A dermatoscopic image of a skin lesion.
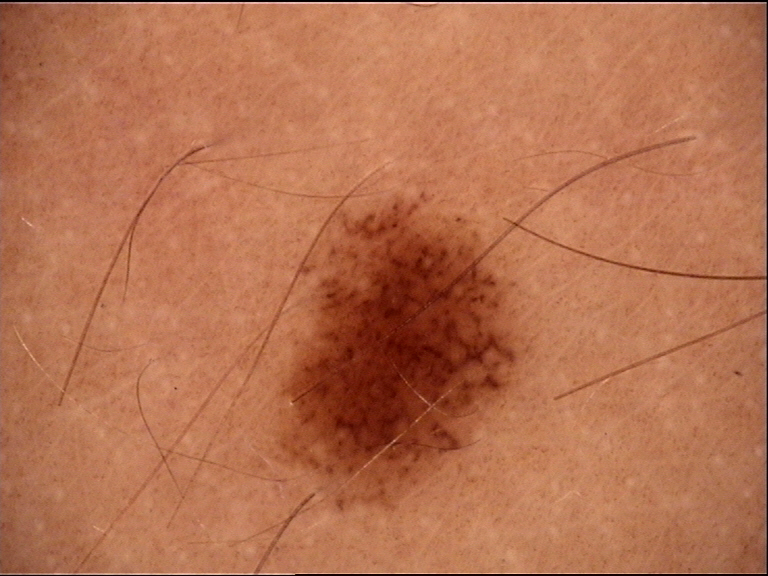diagnosis = dysplastic junctional nevus (expert consensus)